An image taken at a distance, the condition has been present for three to twelve months, reported lesion symptoms include itching, no associated systemic symptoms reported, the leg is involved, the patient considered this a rash, the lesion is described as raised or bumpy and rough or flaky.
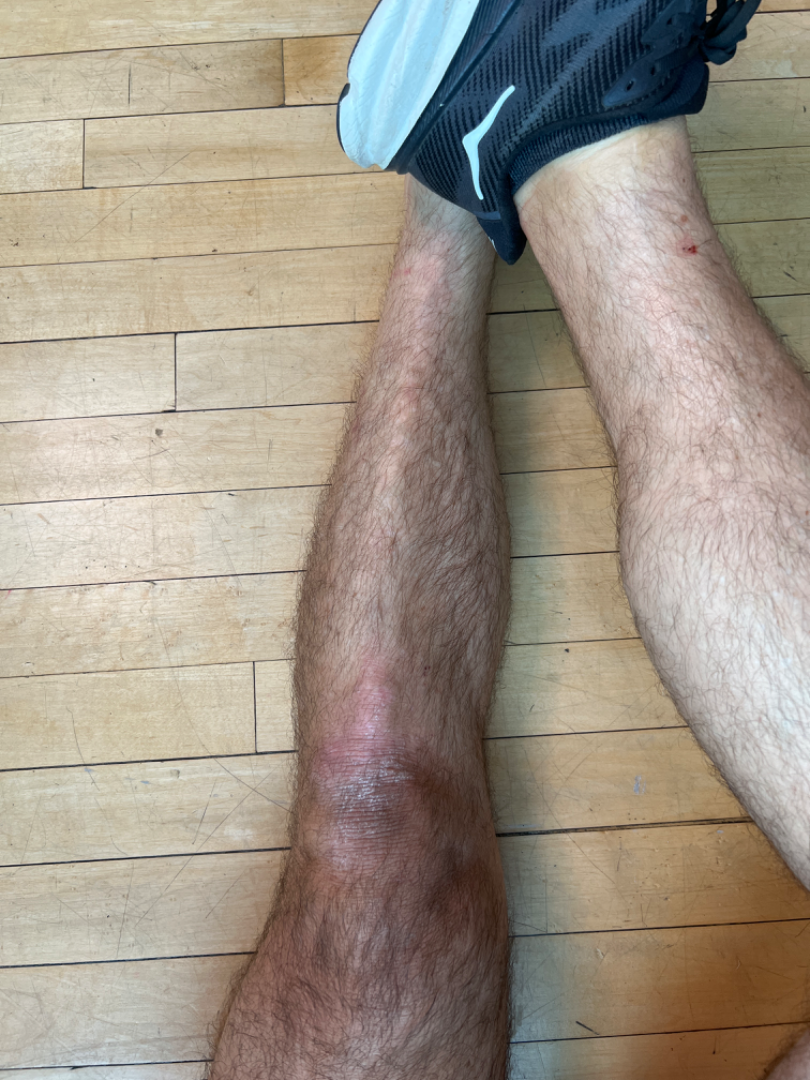The reviewing clinician's impression was: Psoriasis (primary).